A male subject, aged around 40 · a dermoscopy image of a single skin lesion — 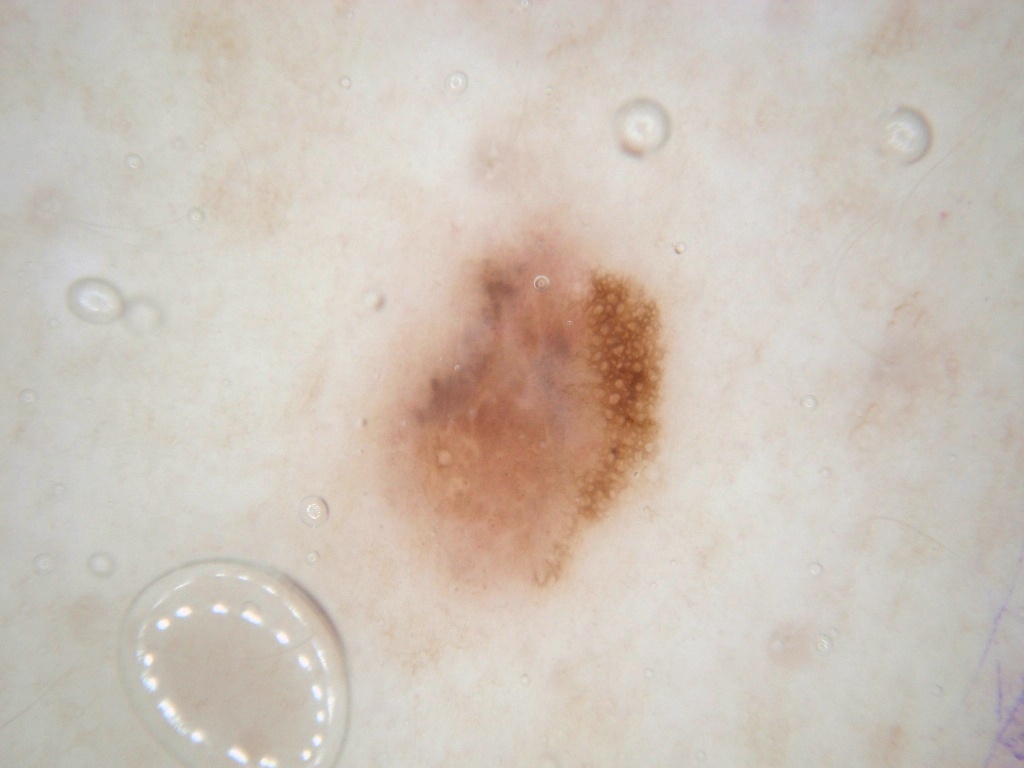The lesion occupies the region bbox(369, 214, 667, 592). Dermoscopy demonstrates negative network and pigment network; no milia-like cysts, globules, or streaks. The lesion takes up a moderate portion of the field. The clinical diagnosis was a melanocytic nevus.